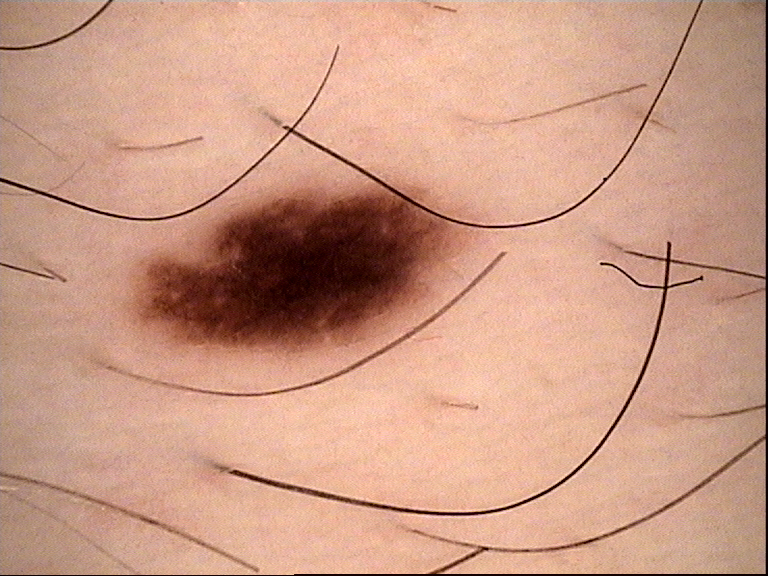Conclusion:
The diagnostic label was a dysplastic junctional nevus.